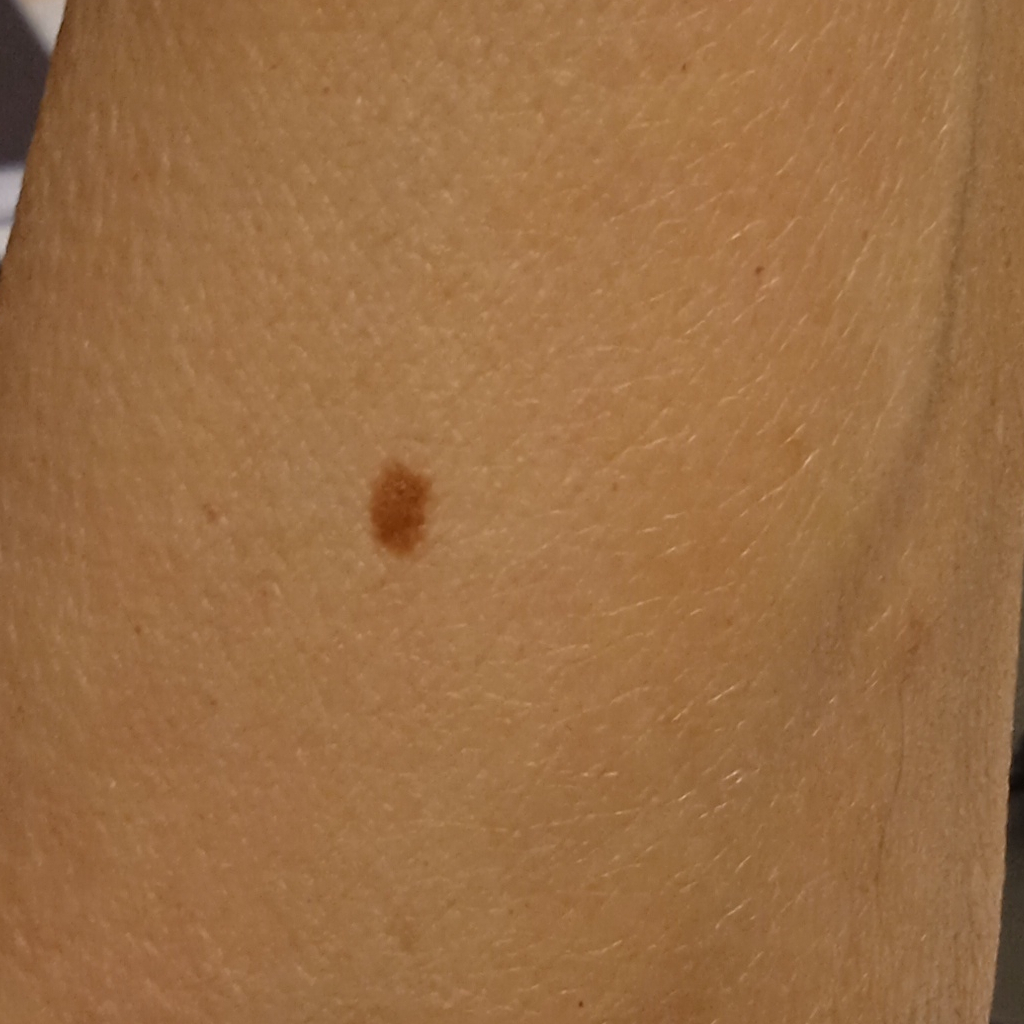sun reaction=skin tans without first burning | image type=clinical photo | nevus count=few melanocytic nevi overall | patient=female, age 67 | body site=an arm | size=4.9 mm | assessment=melanocytic nevus (dermatologist consensus).